The patient indicates darkening, bothersome appearance, enlargement and itching · the patient considered this a rash · the photograph was taken at a distance · the lesion involves the head or neck, arm and front of the torso · texture is reported as raised or bumpy and rough or flaky · reported duration is one to three months: 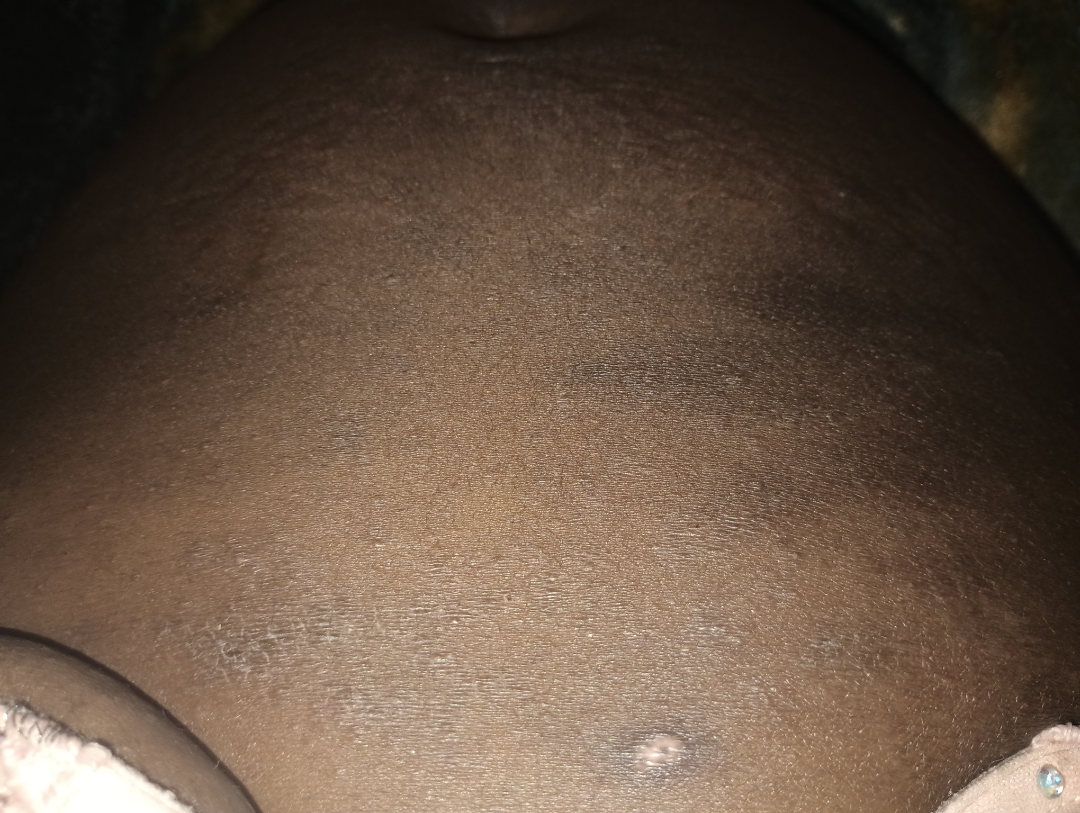{"assessment": "indeterminate from the photograph"}